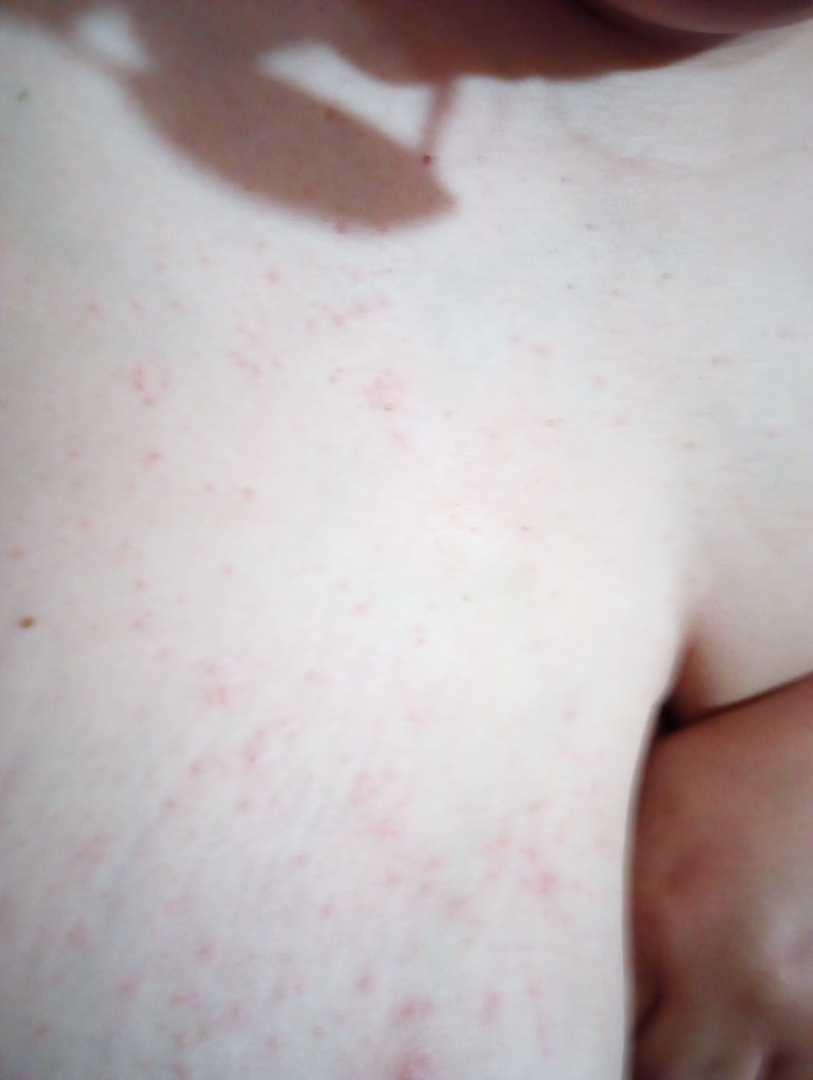<summary>
  <assessment>not assessable</assessment>
  <patient_category>a rash</patient_category>
  <duration>about one day</duration>
  <symptoms>itching</symptoms>
  <texture>raised or bumpy</texture>
  <patient>female, age 40–49</patient>
  <shot_type>close-up</shot_type>
</summary>